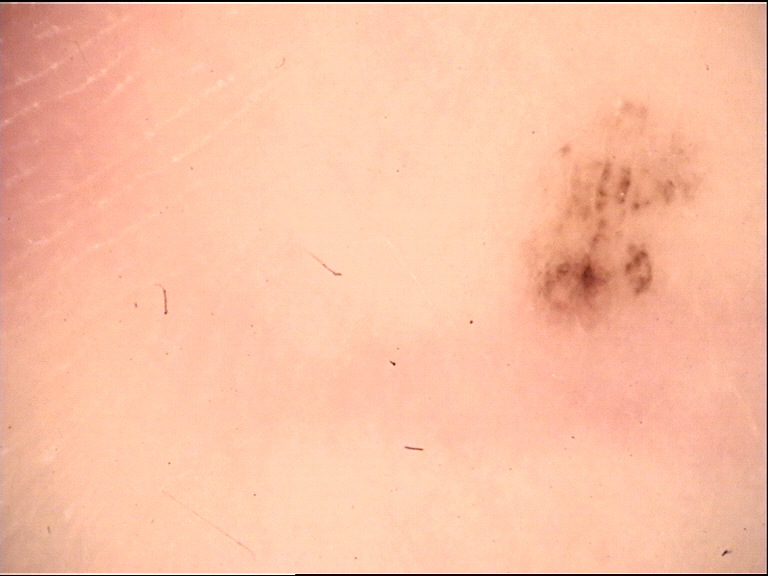This is a banal lesion. Labeled as an acral junctional nevus.